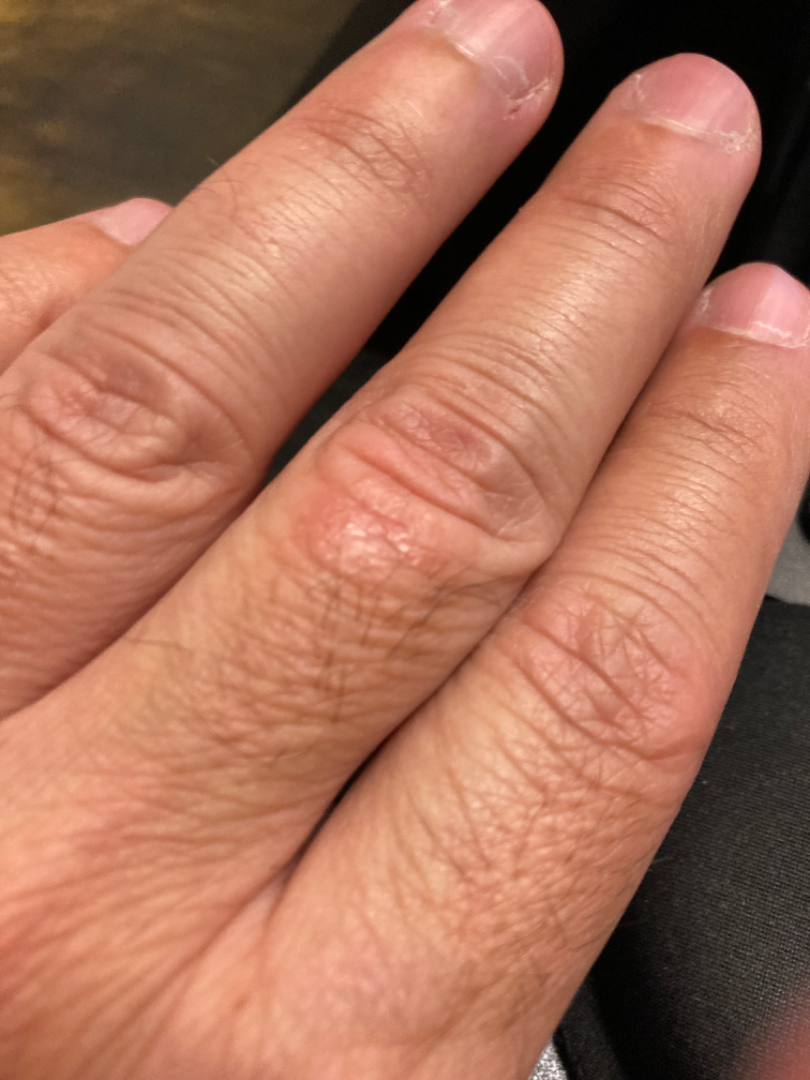Assessment: The skin condition could not be confidently assessed from this image. Clinical context: The patient is 50–59, male. Self-categorized by the patient as a rash. The lesion involves the back of the hand. Close-up view. The contributor notes the condition has been present for one to four weeks. Texture is reported as raised or bumpy. The contributor notes itching.